A dermoscopy image of a single skin lesion.
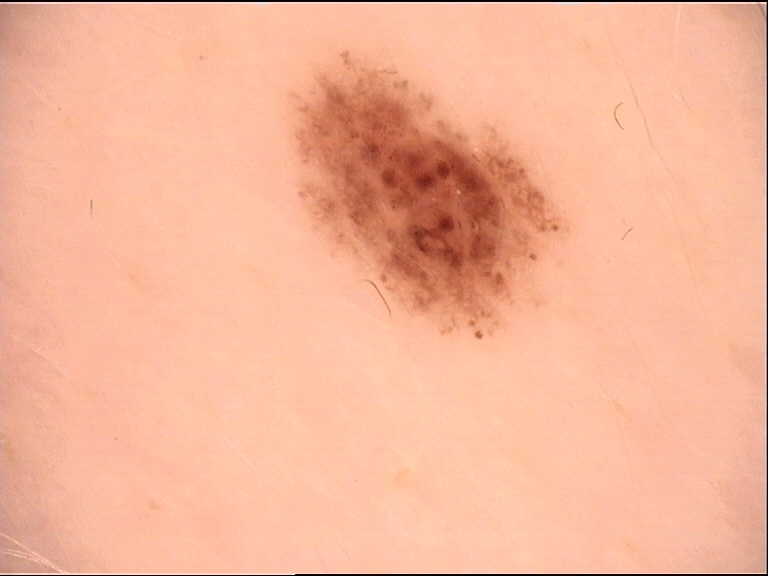Q: What is this lesion?
A: dysplastic junctional nevus (expert consensus)